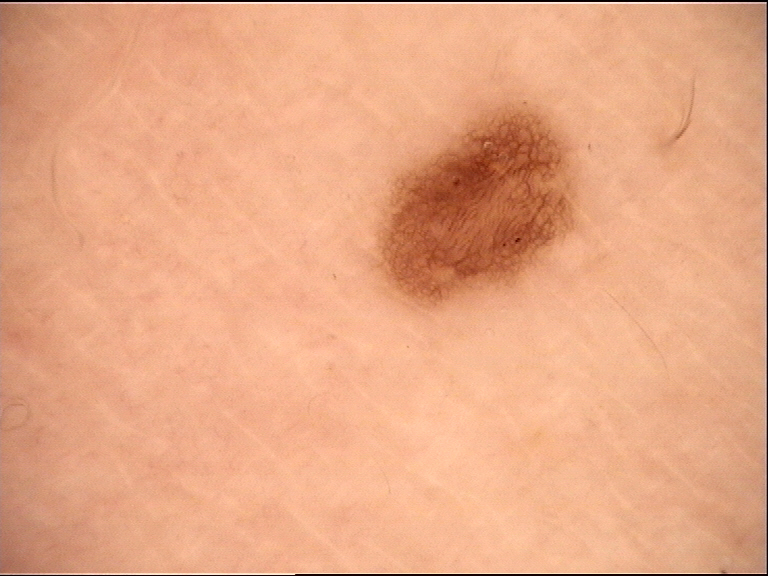Q: What is the imaging modality?
A: dermatoscopy
Q: What was the diagnostic impression?
A: dysplastic junctional nevus (expert consensus)